A dermoscopic image of a skin lesion: 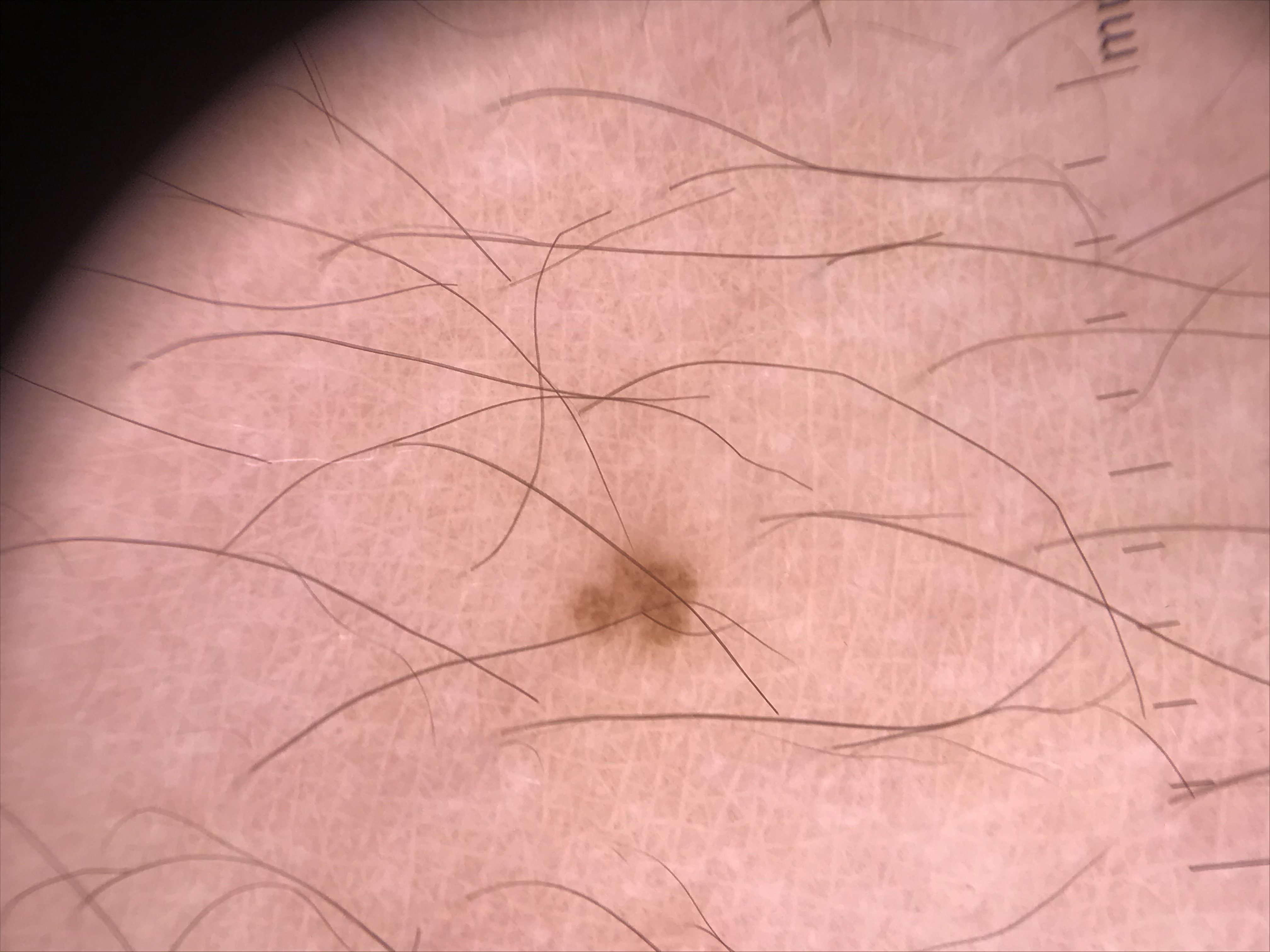• label: junctional nevus (expert consensus)